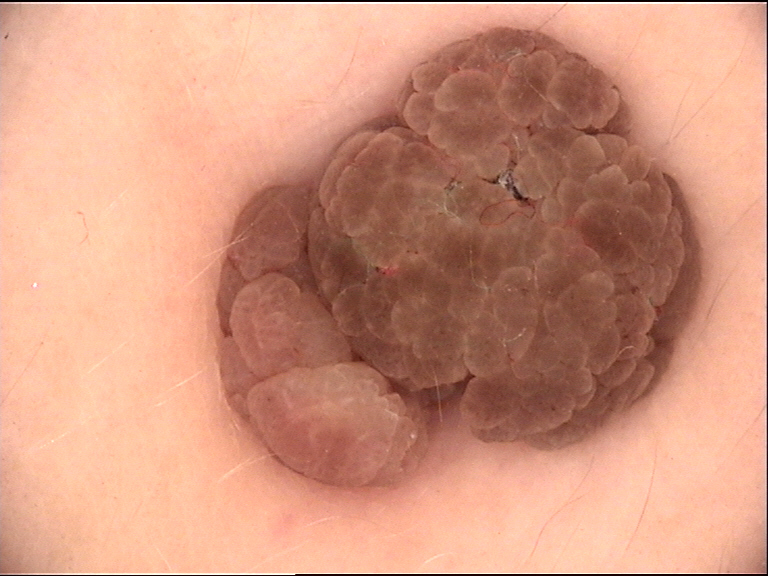{"image": "dermatoscopy", "diagnosis": {"name": "dermal nevus", "code": "db", "malignancy": "benign", "super_class": "melanocytic", "confirmation": "expert consensus"}}